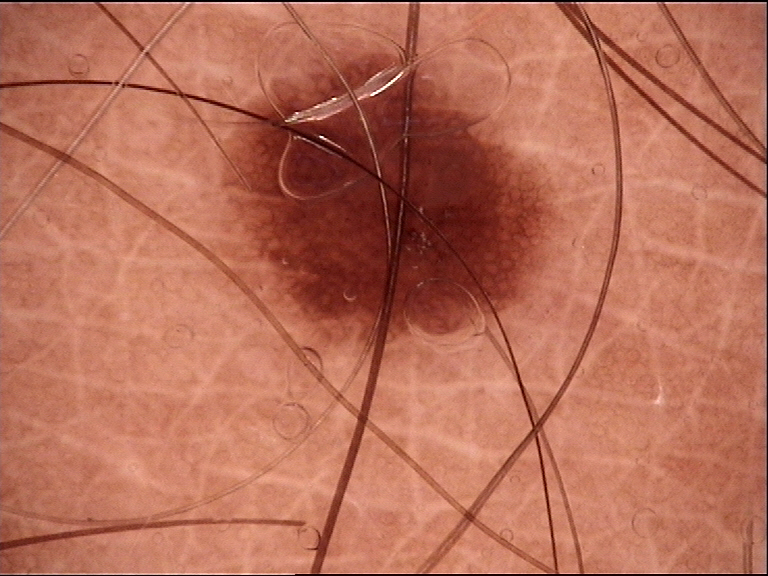– assessment: junctional nevus (expert consensus)